A dermoscopic close-up of a skin lesion.
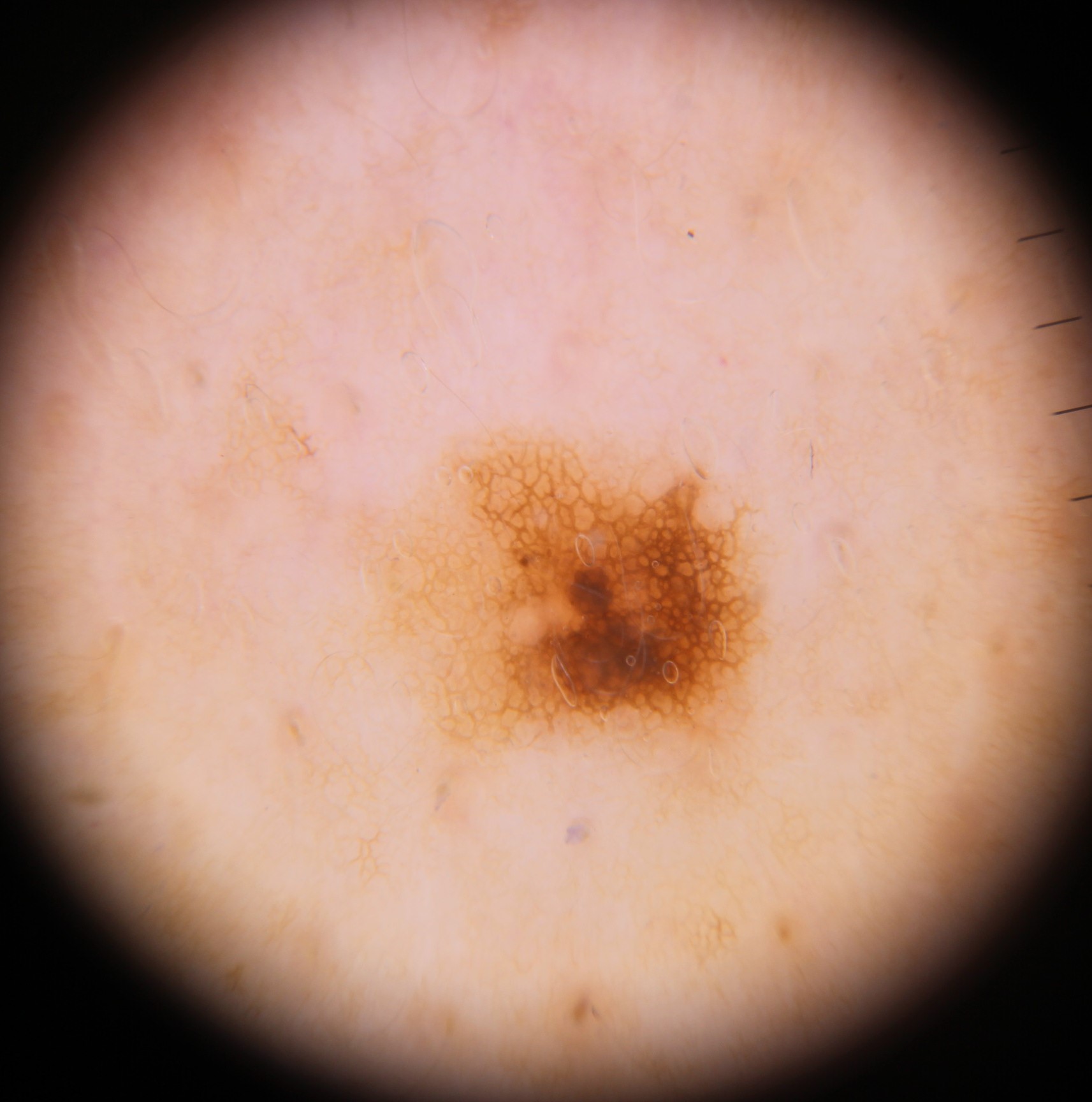{
  "diagnosis": {
    "name": "dysplastic junctional nevus",
    "code": "jd",
    "malignancy": "benign",
    "super_class": "melanocytic",
    "confirmation": "expert consensus"
  }
}